A dermoscopy image of a single skin lesion. A male patient, about 35 years old:
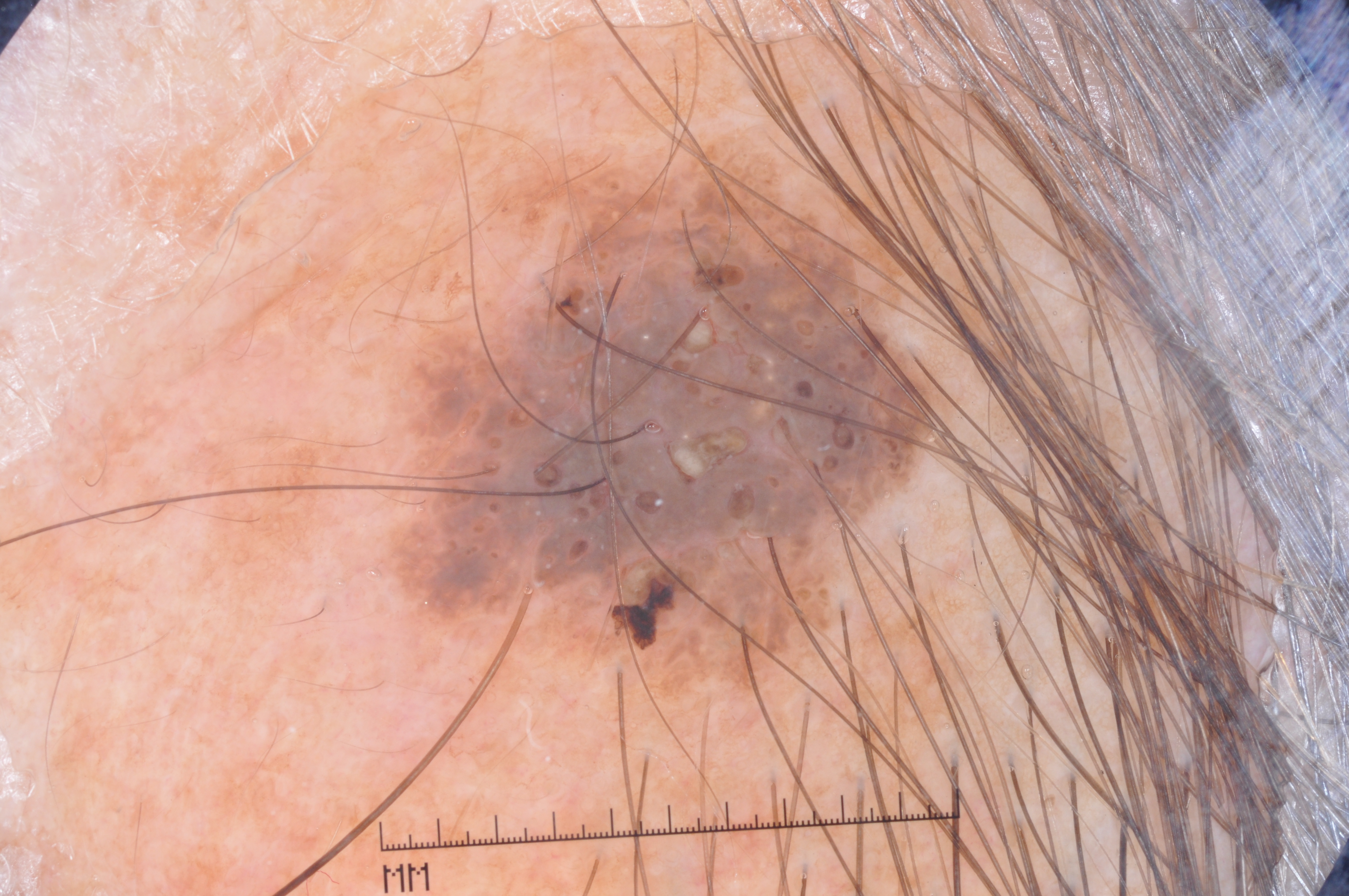The lesion takes up about 27% of the image. Dermoscopic review identifies milia-like cysts. The lesion's extent is left=321, top=105, right=965, bottom=747. Diagnosed as a seborrheic keratosis.